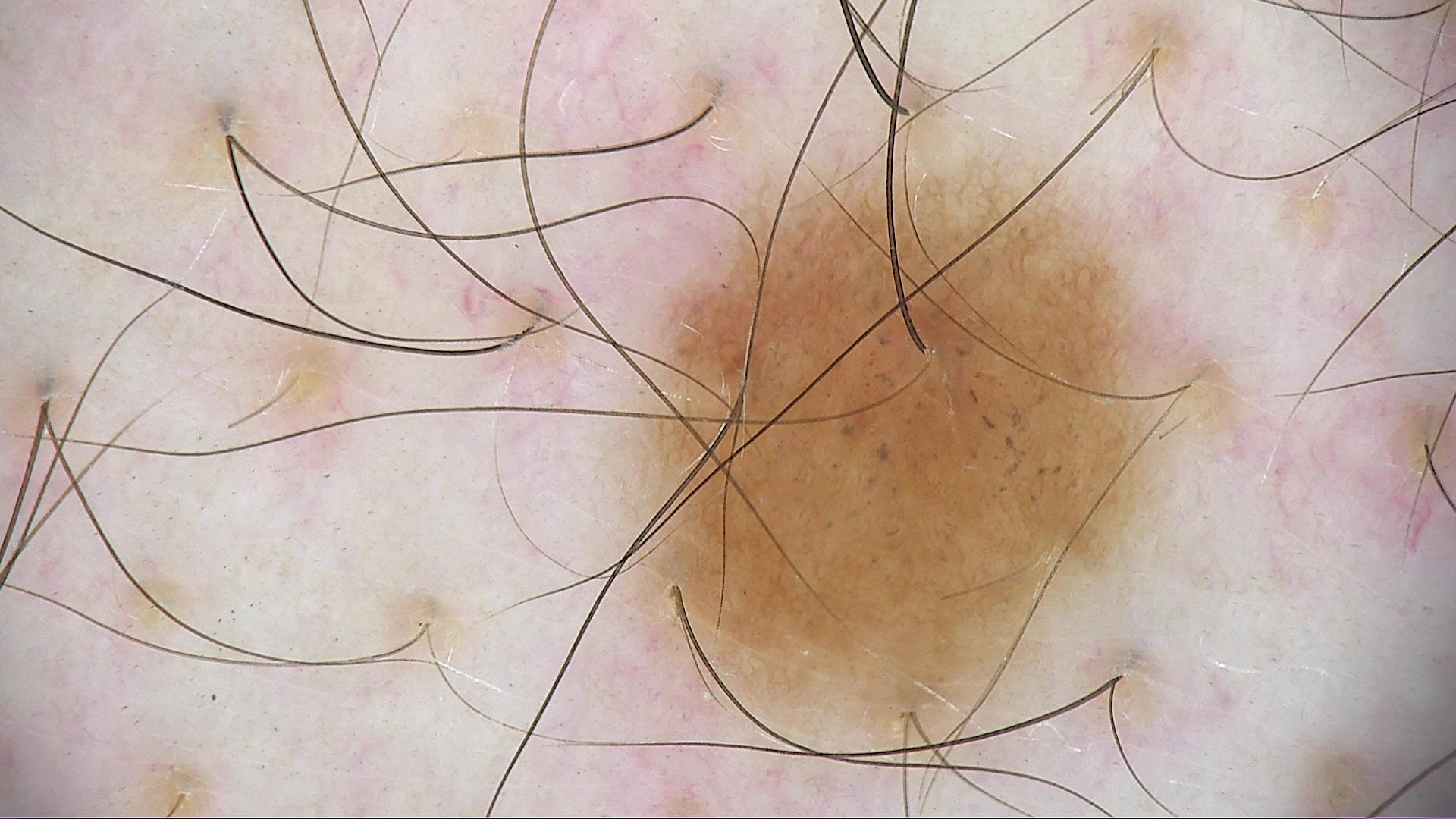| field | value |
|---|---|
| imaging | dermatoscopy |
| assessment | dysplastic junctional nevus (expert consensus) |